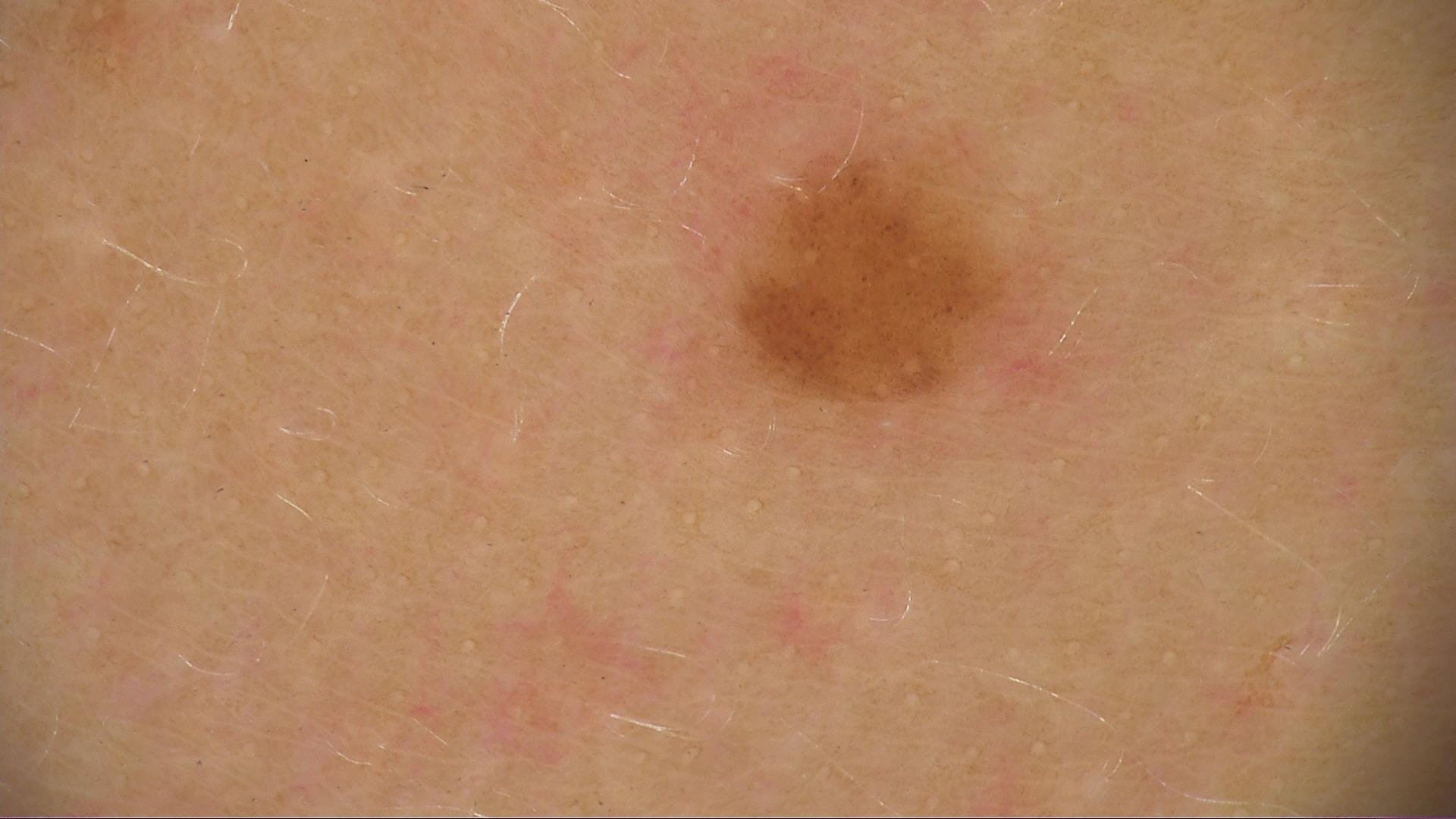| field | value |
|---|---|
| image | dermoscopy |
| diagnostic label | junctional nevus (expert consensus) |